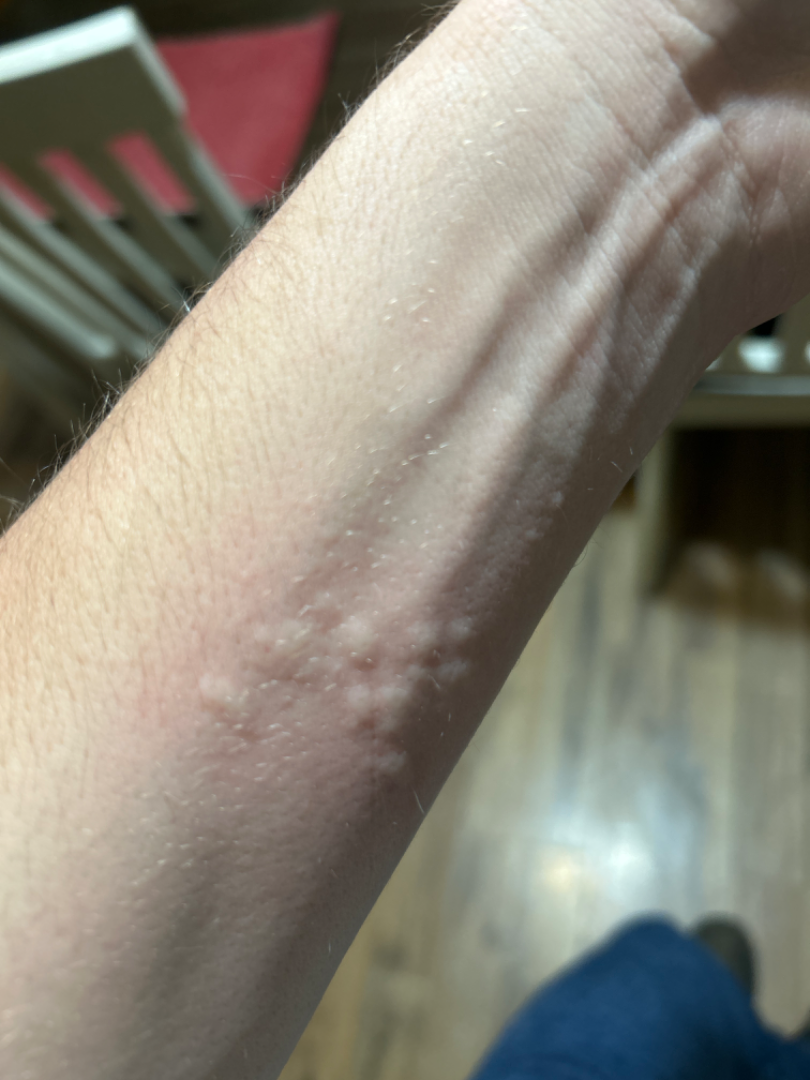Notes:
- photo taken · at an angle
- dermatologist impression · consistent with Urticaria